The patient also reports mouth sores; the patient notes darkening, pain, burning, itching and bothersome appearance; this is a close-up image; the patient notes the lesion is raised or bumpy; the patient described the issue as a nail problem; located on the arm, head or neck, back of the torso and back of the hand.
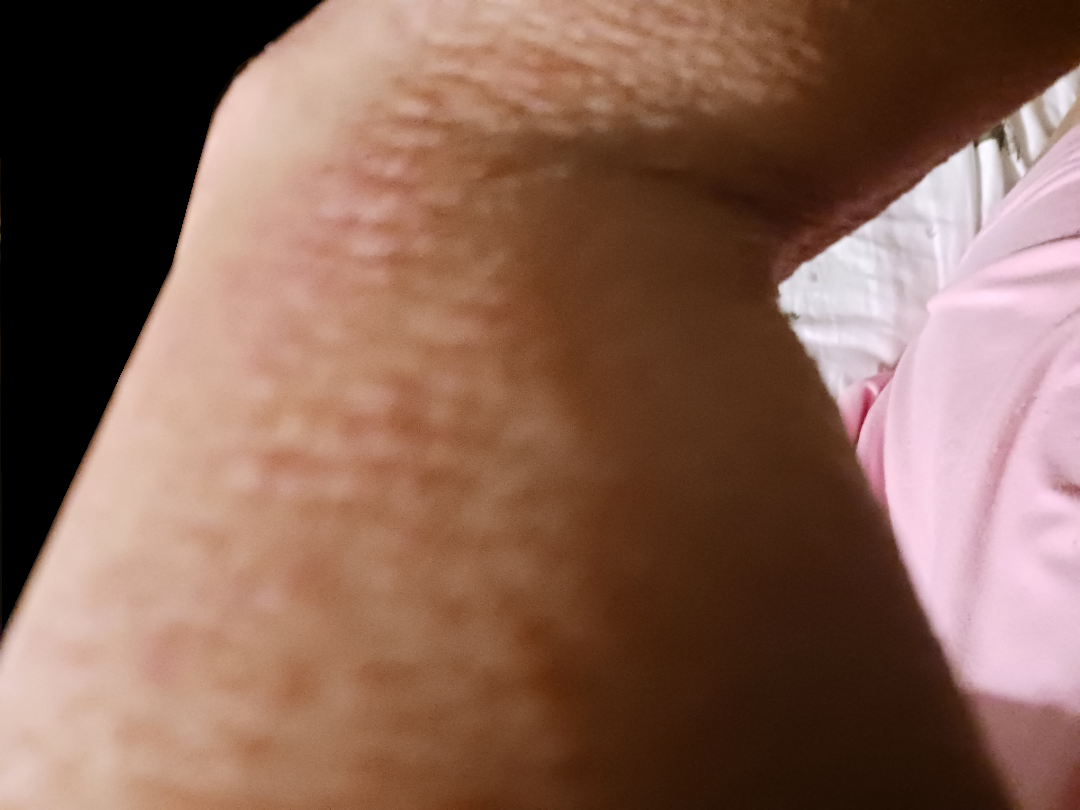assessment: indeterminate from the photograph.